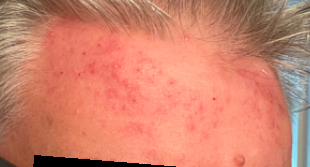History: Located on the head or neck. Present for more than one year. Male subject, age 50–59. An image taken at a distance. No constitutional symptoms were reported. Self-categorized by the patient as a rash. The lesion is associated with bothersome appearance. Impression: On remote review of the image: consistent with Rosacea.